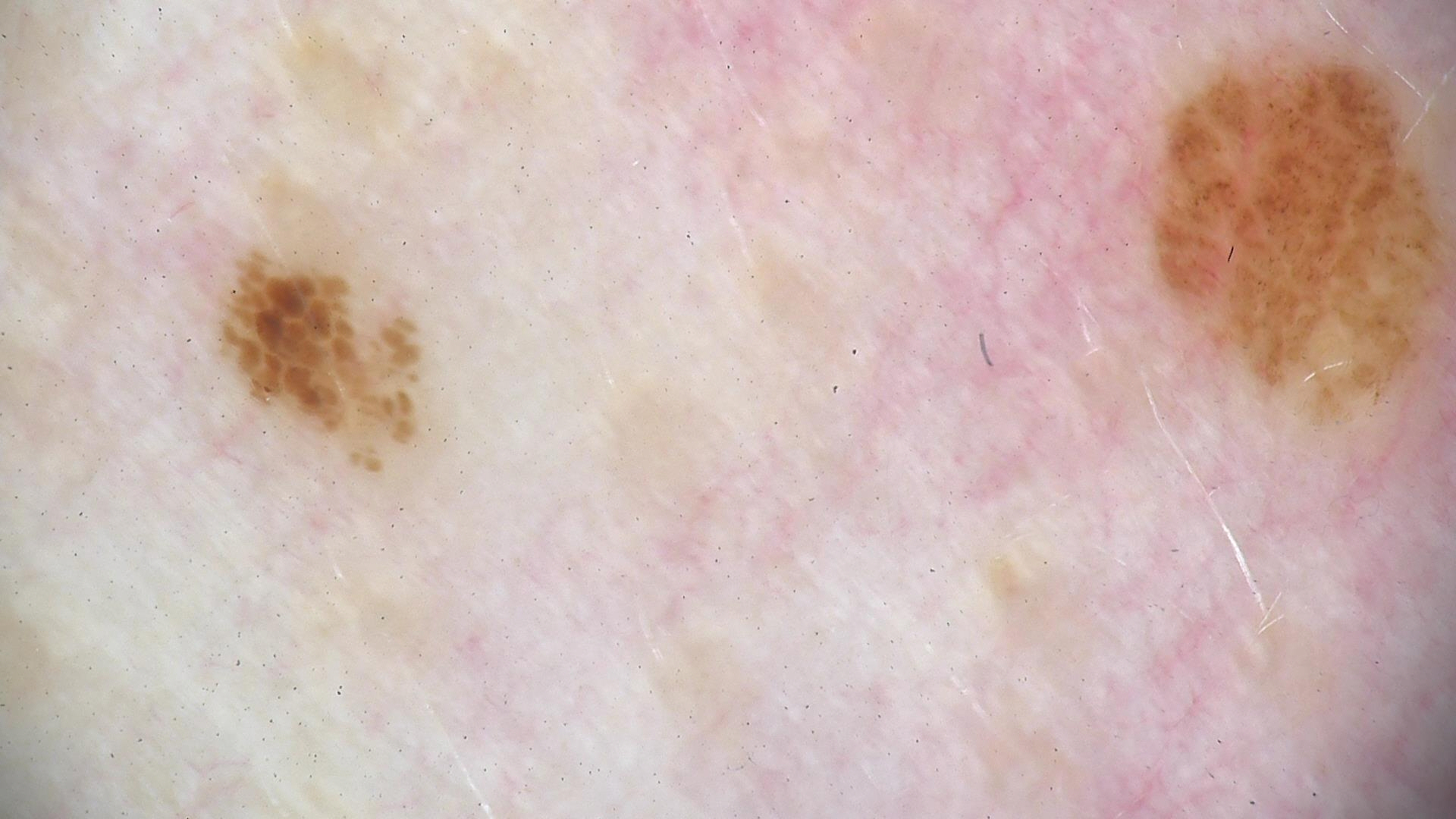modality: dermatoscopy; assessment: dysplastic junctional nevus (expert consensus).